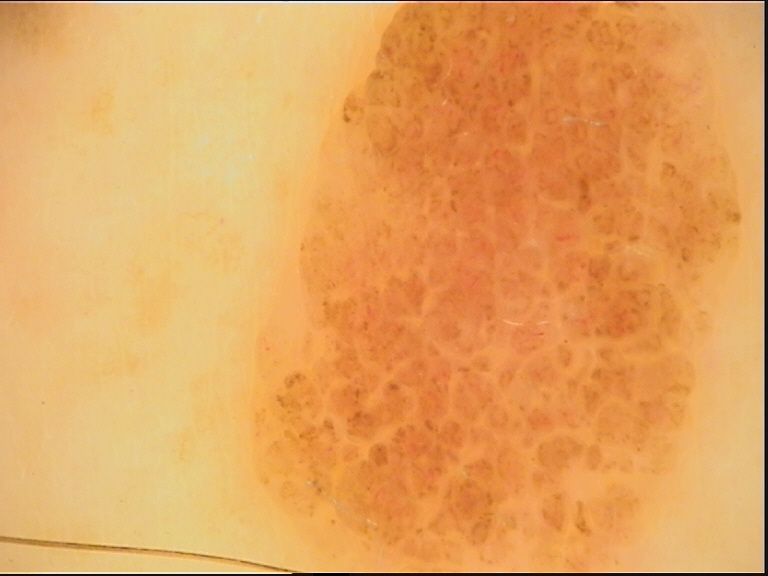Conclusion:
Classified as a compound nevus.